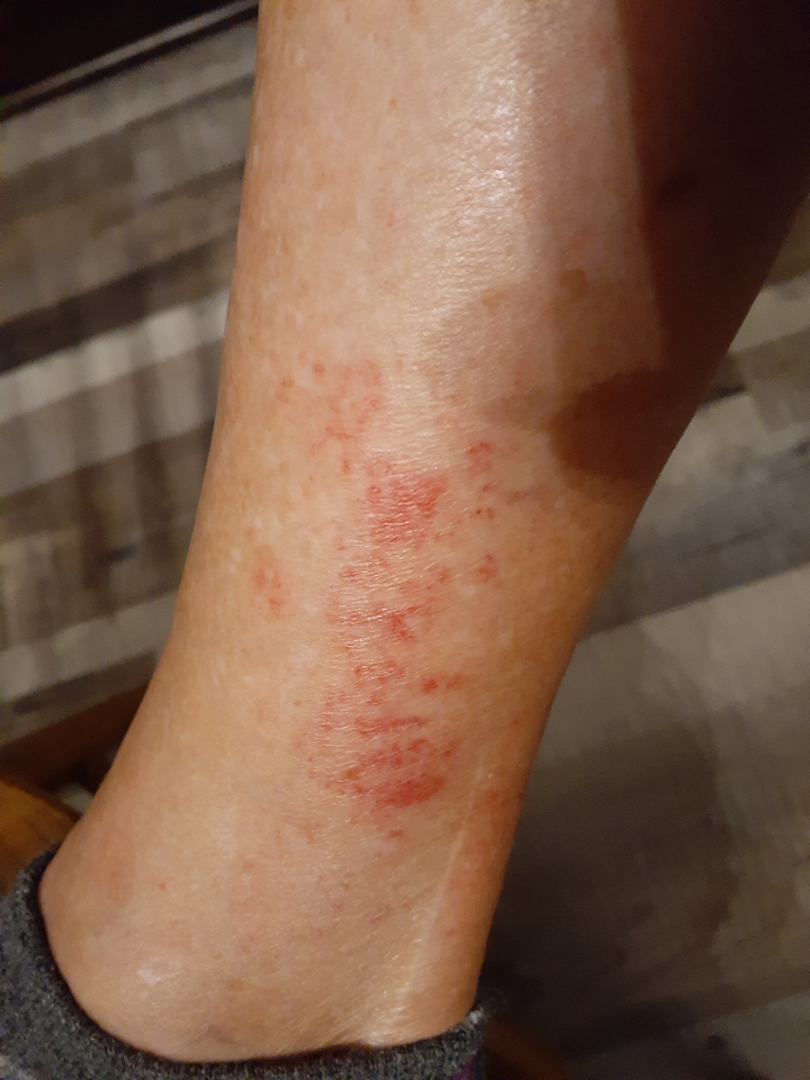The reviewer's impression was Eczema.